The patient reports immunosuppression, a personal history of skin cancer, and a personal history of cancer · a female subject age 72 · imaged for a research study, with no referral diagnosis recorded · a moderate number of moles by the patient's own estimate · the patient says their skin reddens painfully with sun exposure: 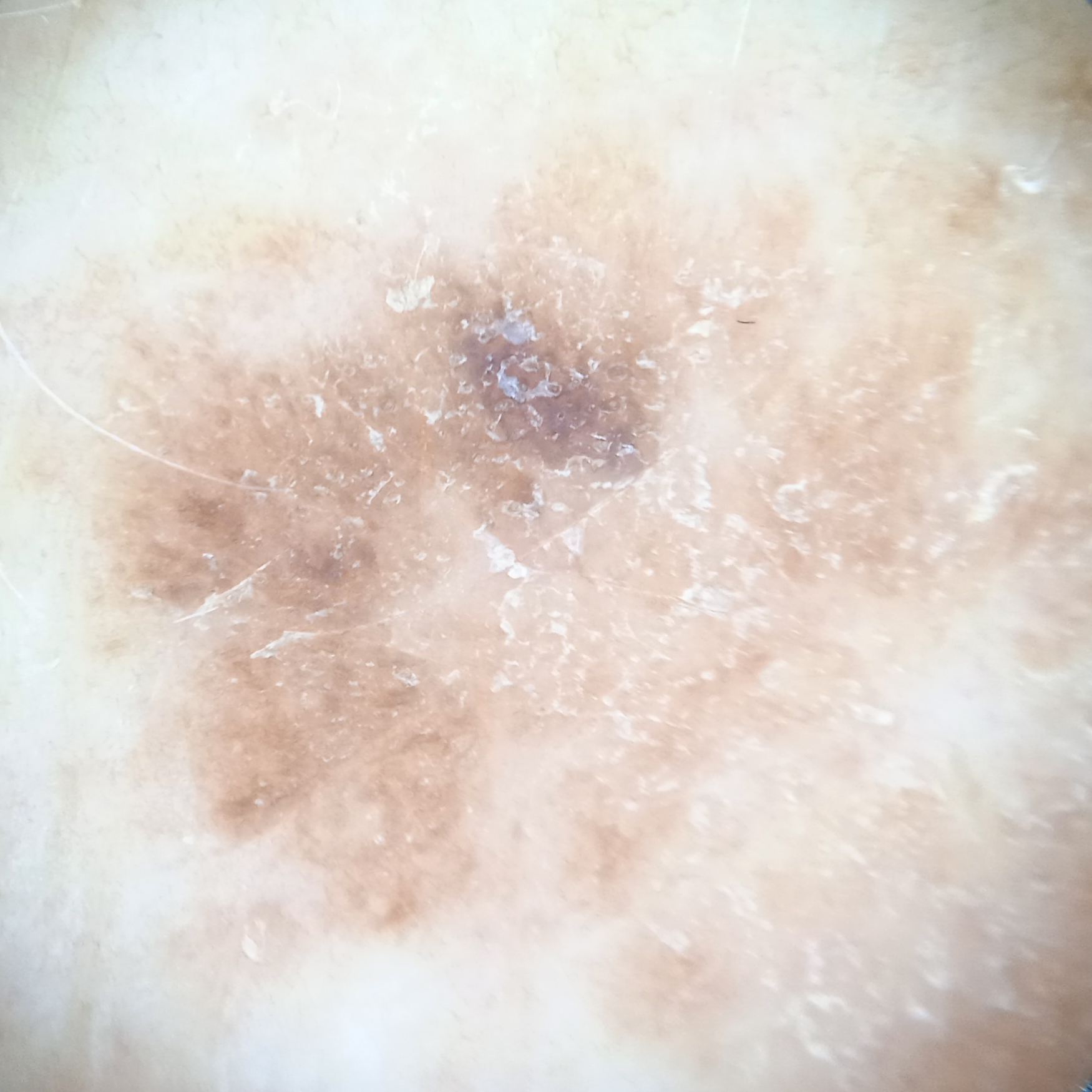  lesion_size:
    diameter_mm: 13.8
  diagnosis:
    name: seborrheic keratosis
    malignancy: benign
    unanimous: true
    certainty: moderate
    second_options:
      - a melanoma or melanocytic nevus